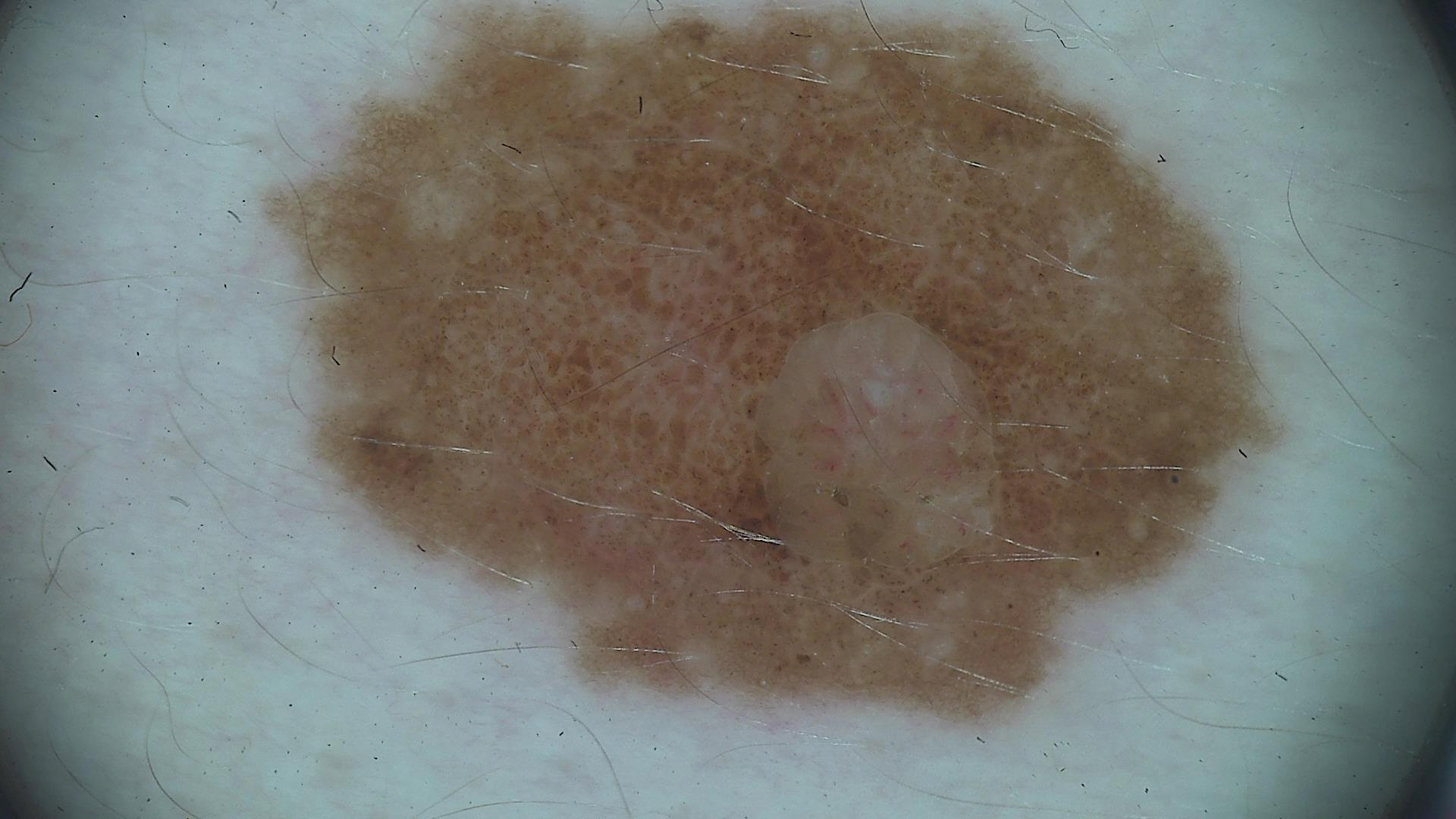Classified as a dysplastic compound nevus.